Dermoscopy of a skin lesion:
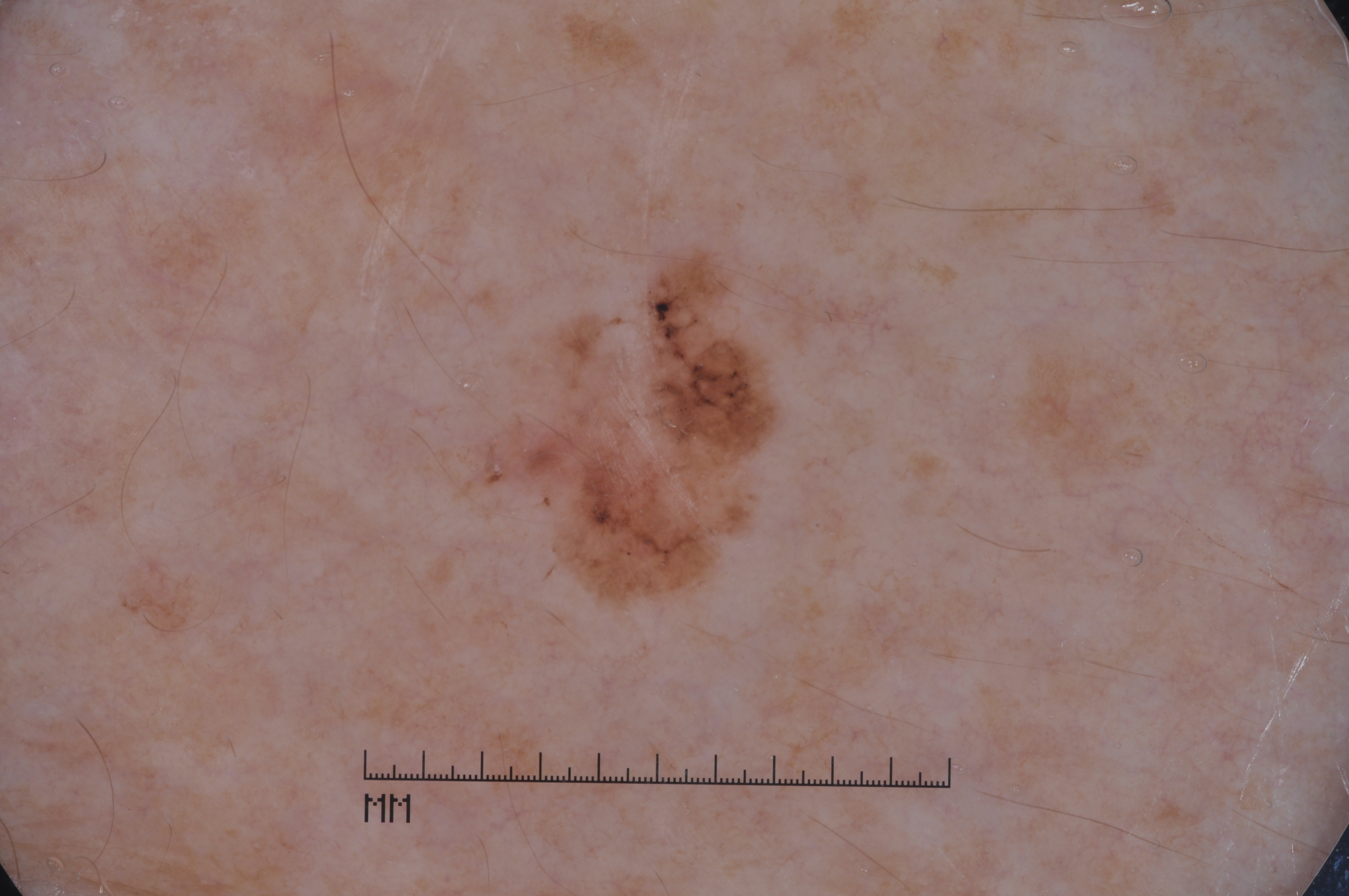The lesion covers approximately 6% of the dermoscopic field. The dermoscopic pattern shows milia-like cysts. The lesion is bounded by bbox=[431, 220, 881, 614]. Histopathologically confirmed as a melanoma.